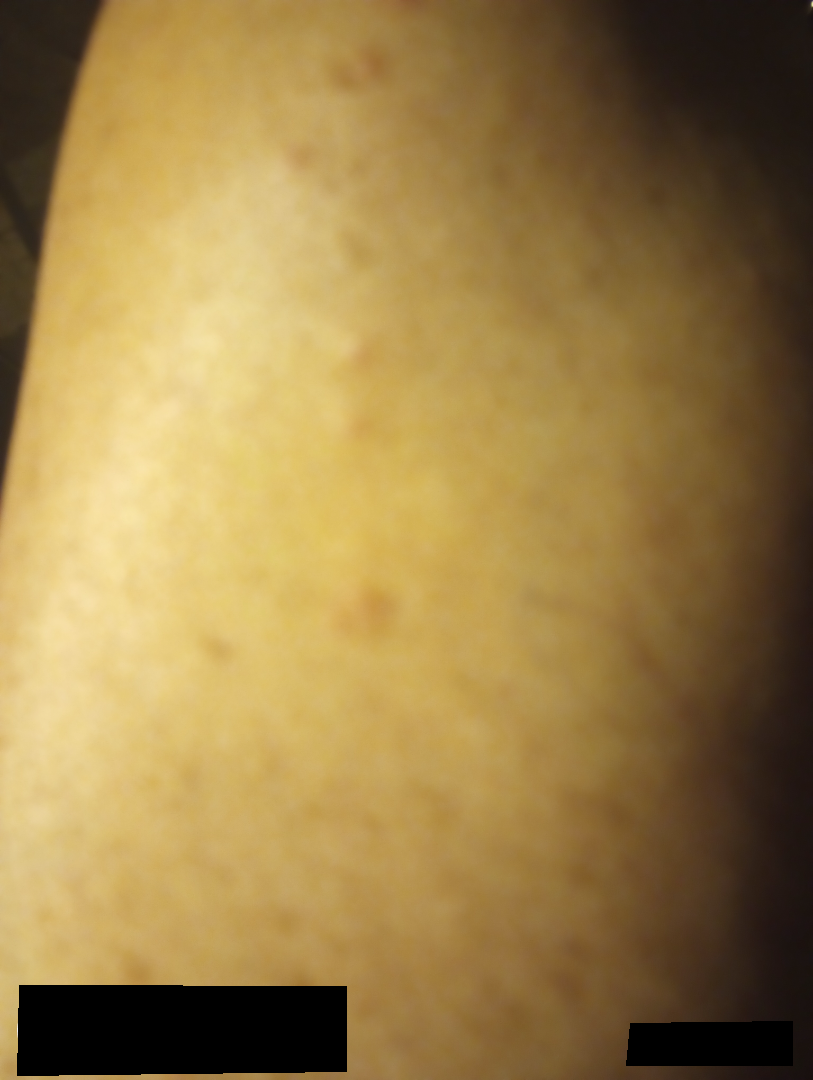The reviewing dermatologist was unable to assign a differential diagnosis from the image.